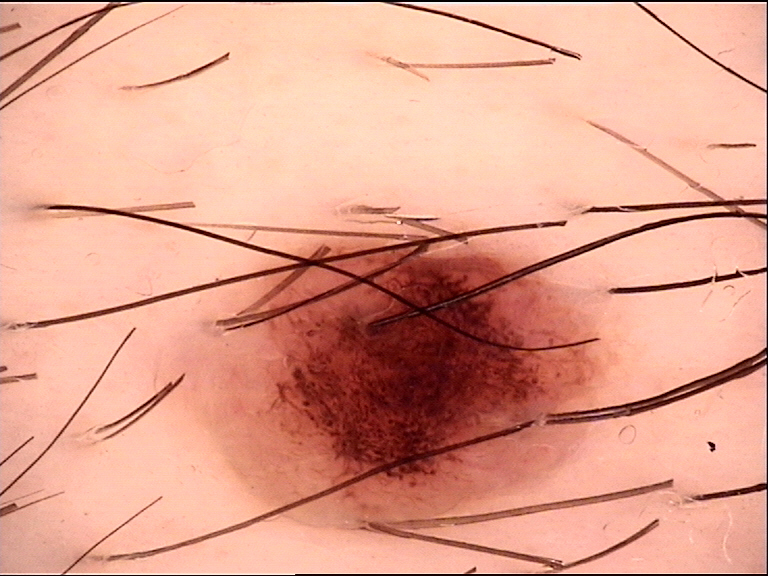The diagnostic label was a compound nevus.